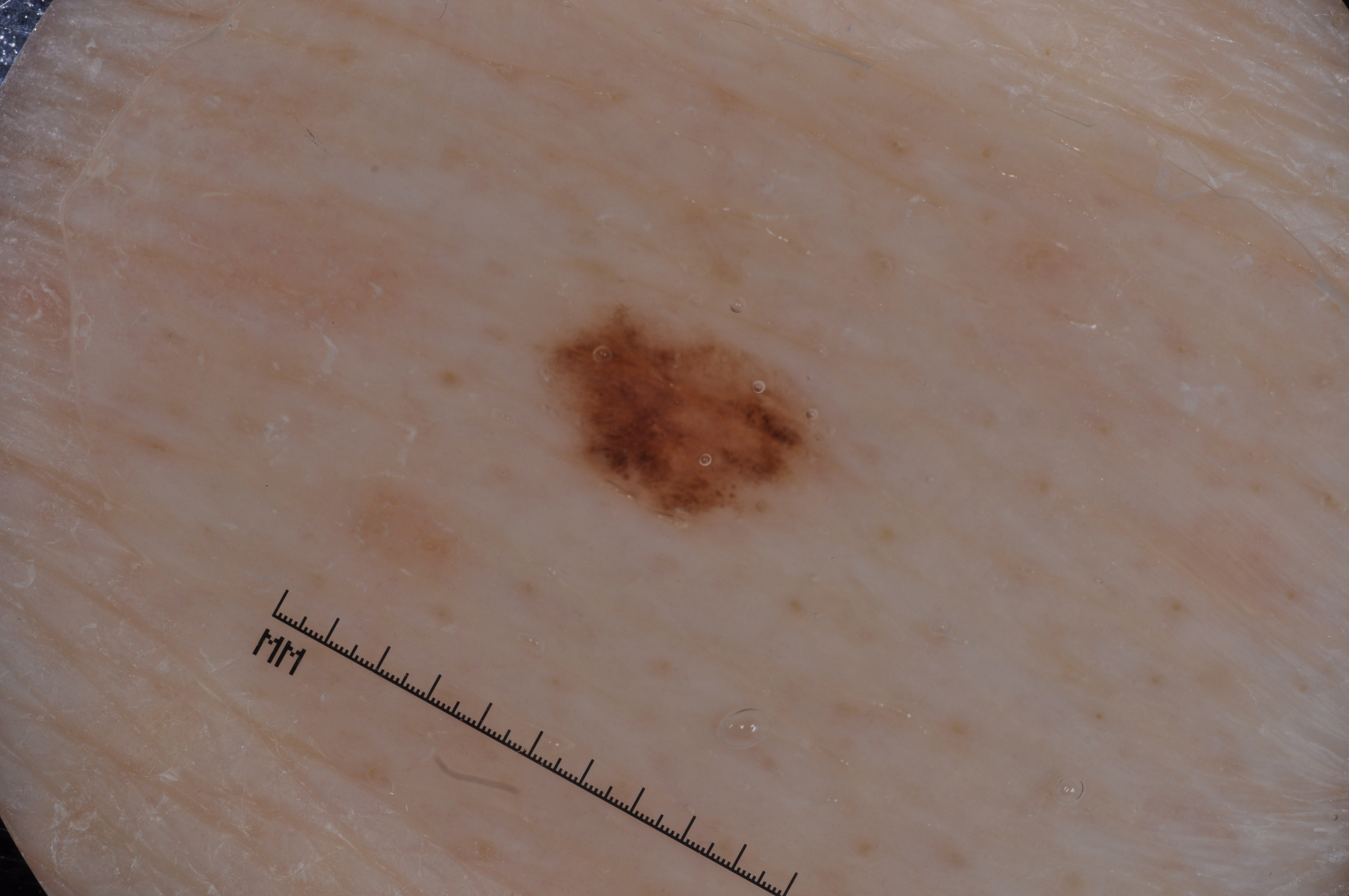Q: What is the imaging modality?
A: dermoscopic image
Q: What are the patient's age and sex?
A: male, approximately 80 years of age
Q: How large is the lesion within the image?
A: ~3% of the field
Q: What dermoscopic features are present?
A: pigment network and milia-like cysts; absent: streaks and negative network
Q: Where is the lesion located?
A: box(548, 309, 822, 525)
Q: What is this lesion?
A: a melanocytic nevus, a benign lesion